A dermatoscopic image of a skin lesion.
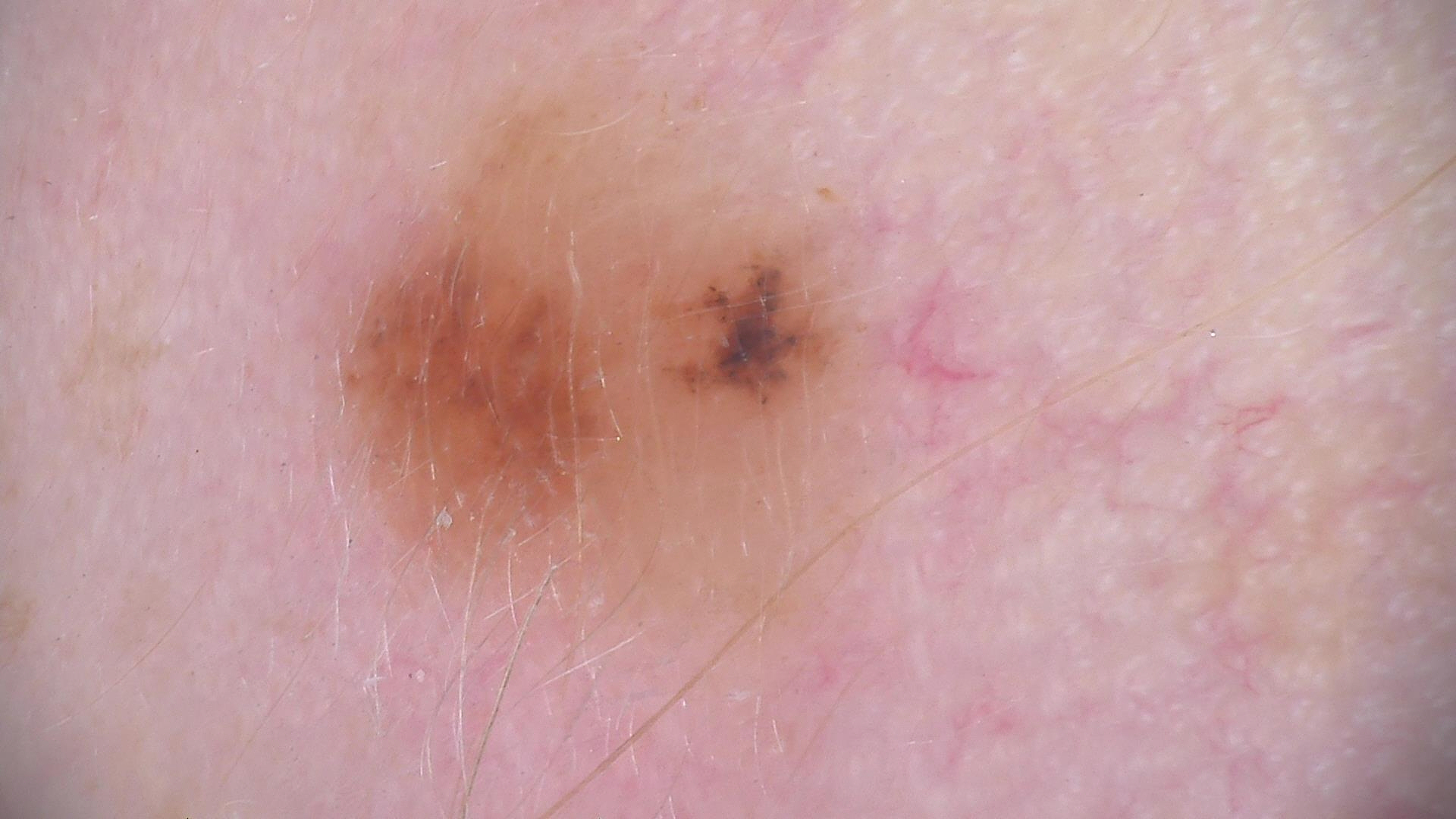Findings:
• assessment: dysplastic compound nevus (expert consensus)